By history, prior skin cancer (patient or family) and prior malignancy (patient or family) · a clinical photograph of a skin lesion · the patient was assessed as Fitzpatrick II:
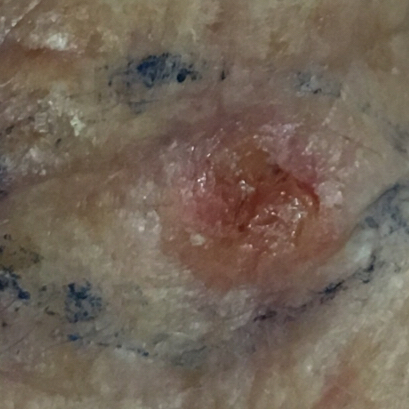region: the nose | lesion diameter: approx. 8 × 7 mm | patient-reported symptoms: pain, elevation, itching, bleeding | diagnostic label: basal cell carcinoma (biopsy-proven).